A skin lesion imaged with a dermatoscope:
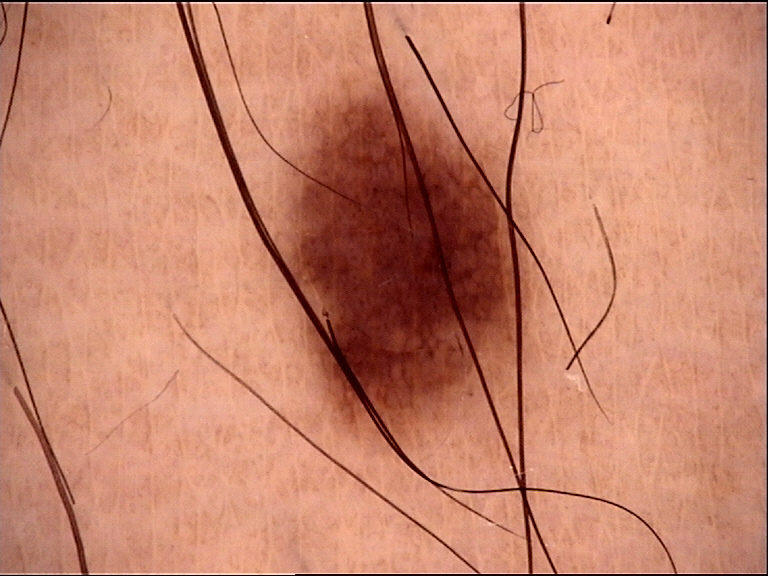The architecture is that of a banal lesion.
The diagnostic label was a junctional nevus.